An image taken at an angle. The leg and arm are involved. The contributor is a female aged 18–29.
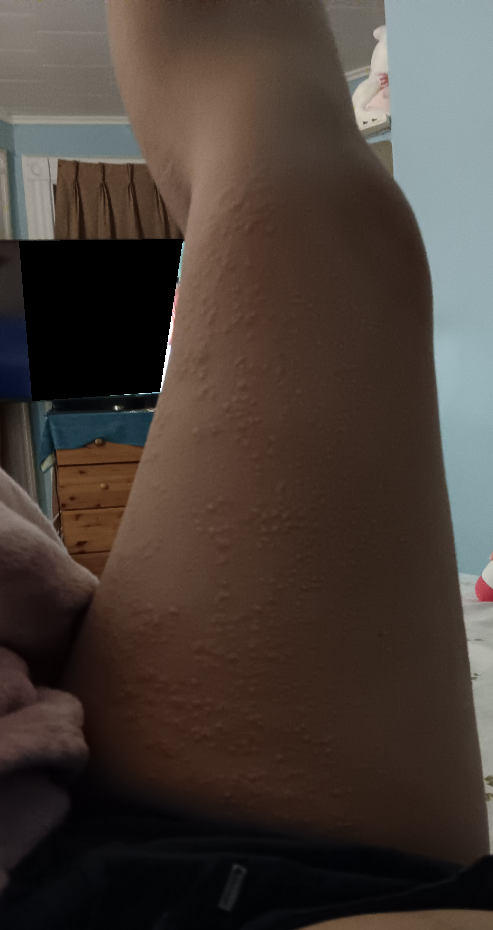On remote review of the image, favoring Eczema.